The patient is a female aged 18–29; located on the head or neck; the photograph is a close-up of the affected area.
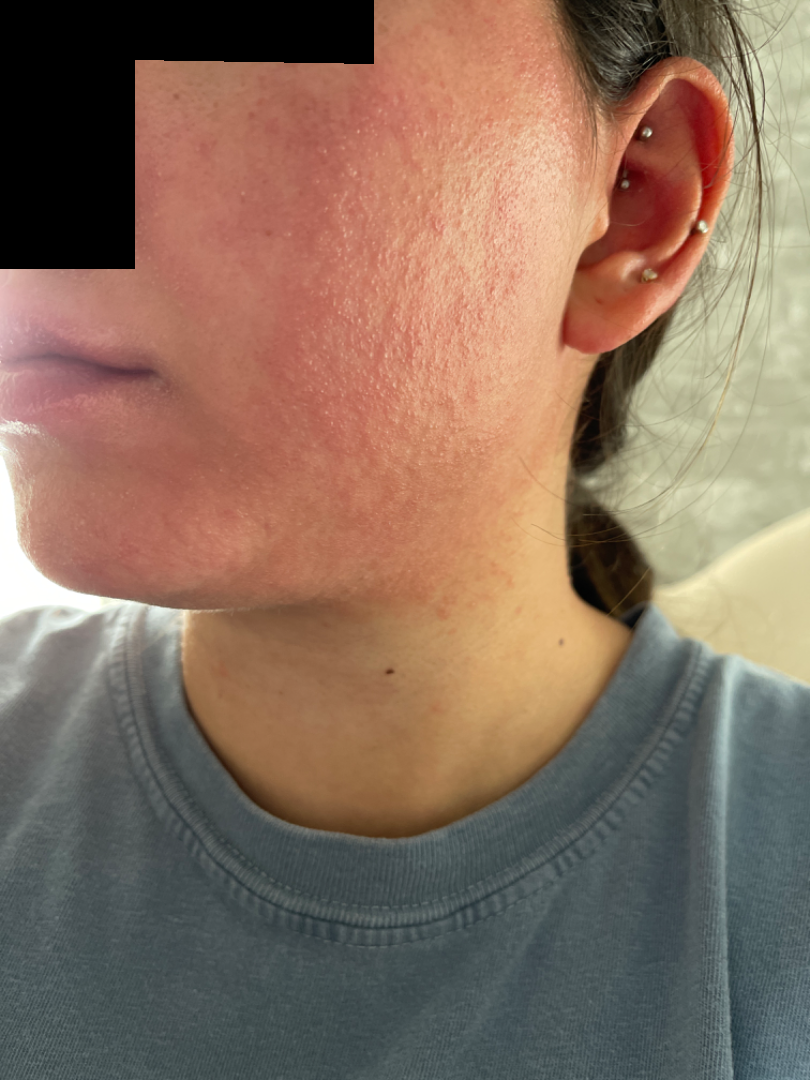Patient information: Texture is reported as raised or bumpy. Symptoms reported: itching and bothersome appearance. Fitzpatrick phototype II; lay graders estimated Monk skin tone scale 3 or 4 (two reviewer pools). The contributor notes the condition has been present for about one day. The contributor notes associated mouth sores. Review: On dermatologist assessment of the image, the primary impression is Allergic Contact Dermatitis; less probable is Eczema; less likely is Keratosis pilaris; a remote consideration is Acne; a more distant consideration is Rosacea.